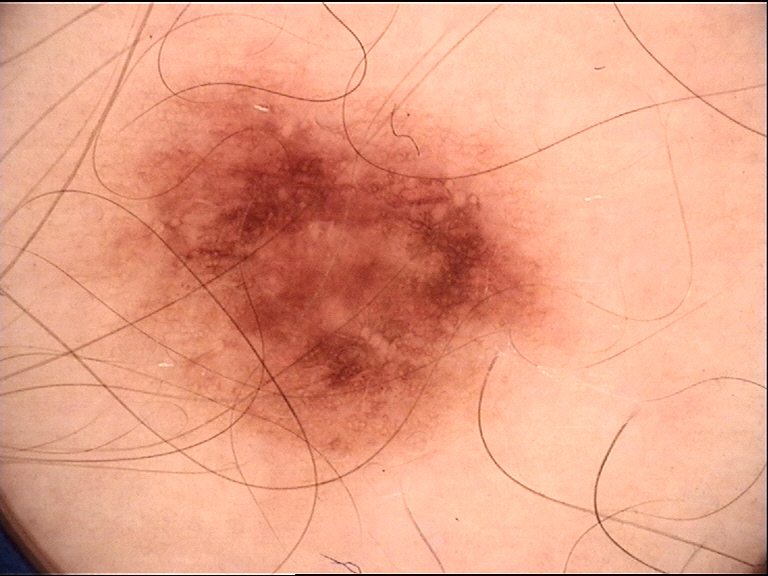Findings: A dermoscopic image of a skin lesion. Impression: Diagnosed as a dysplastic junctional nevus.